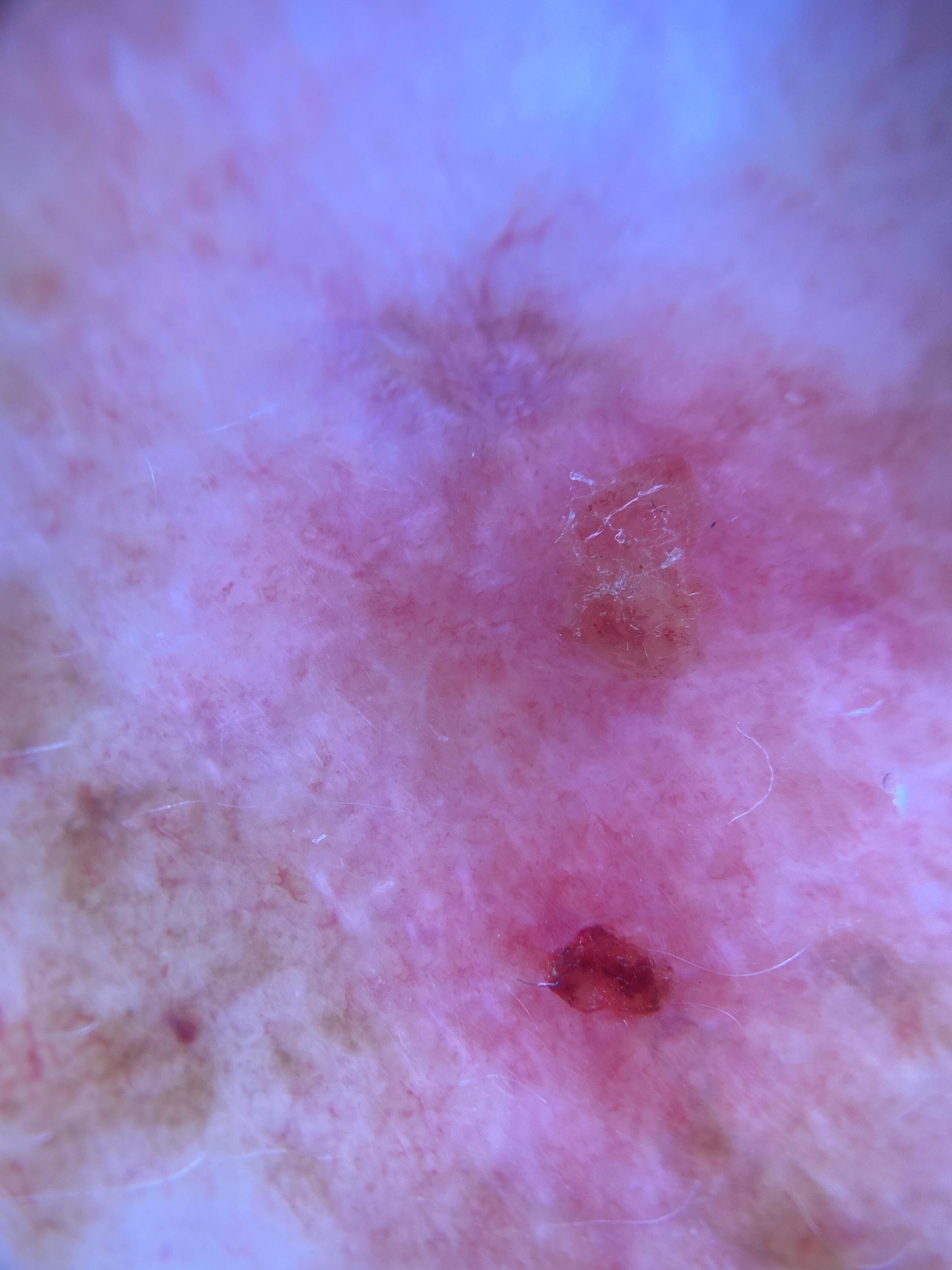modality — dermoscopy | FST — II | subject — female, about 80 years old | location — an upper extremity | pathology — Melanoma (biopsy-proven).